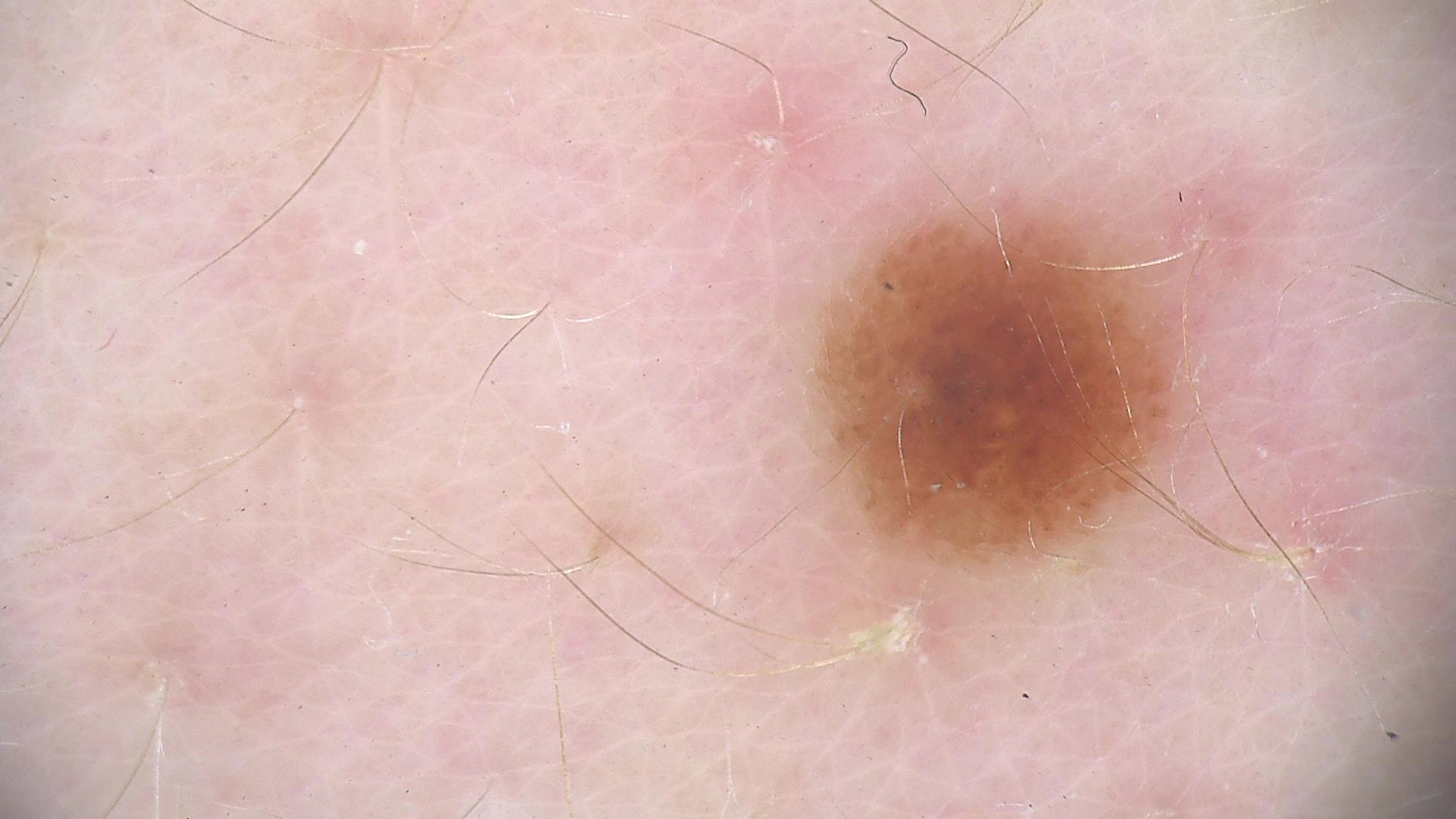Impression: The diagnostic label was a dysplastic junctional nevus.